A male patient in their early 50s. Recorded as Fitzpatrick phototype II. A clinical photo of a skin lesion taken with a smartphone. The chart records prior skin cancer (patient or family) and alcohol use: 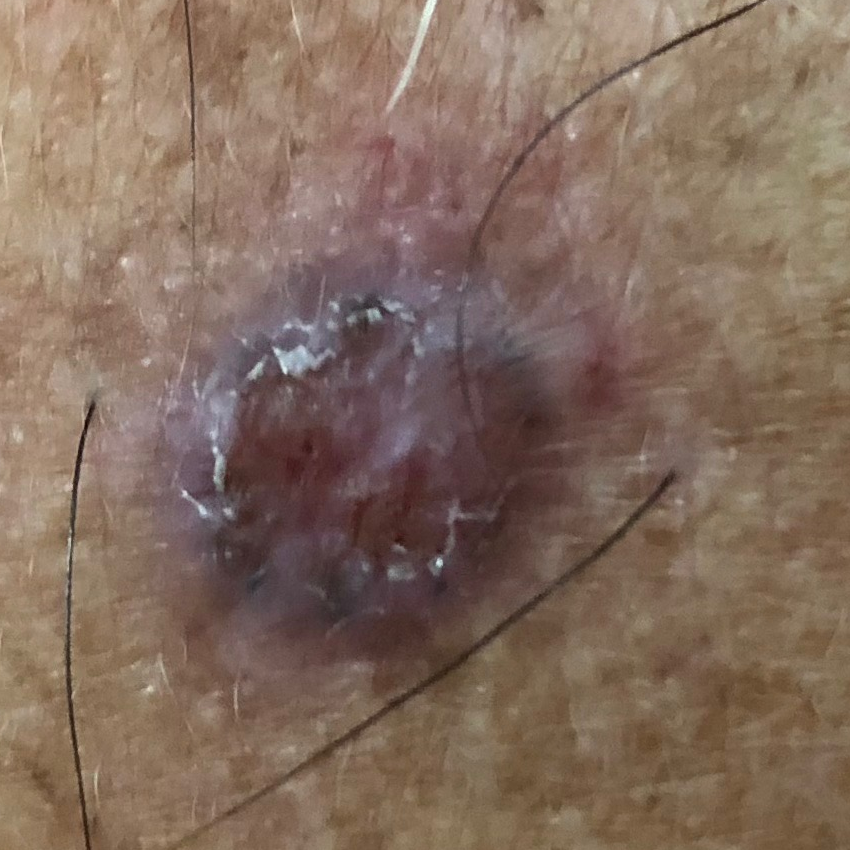Q: How large is the lesion?
A: 12x9 mm
Q: Any reported symptoms?
A: itching, elevation
Q: What did the workup show?
A: basal cell carcinoma (biopsy-proven)